A male patient aged around 85 or older; a skin lesion imaged with a dermatoscope: 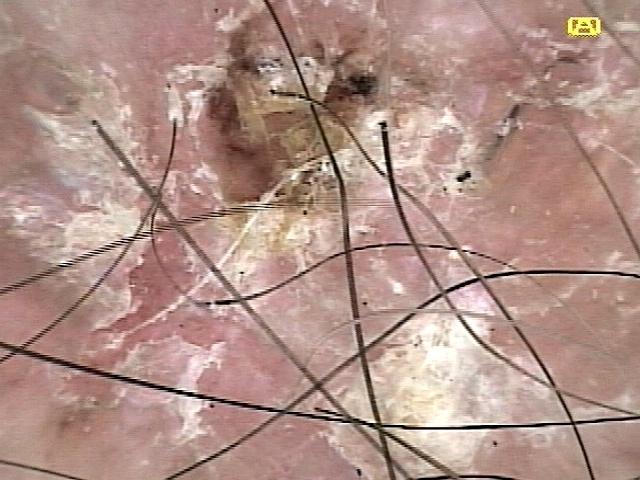<skin_lesion>
  <lesion_location>
    <region>a lower extremity</region>
  </lesion_location>
  <diagnosis>
    <name>Squamous cell carcinoma</name>
    <malignancy>malignant</malignancy>
    <confirmation>histopathology</confirmation>
    <lineage>epidermal</lineage>
  </diagnosis>
</skin_lesion>